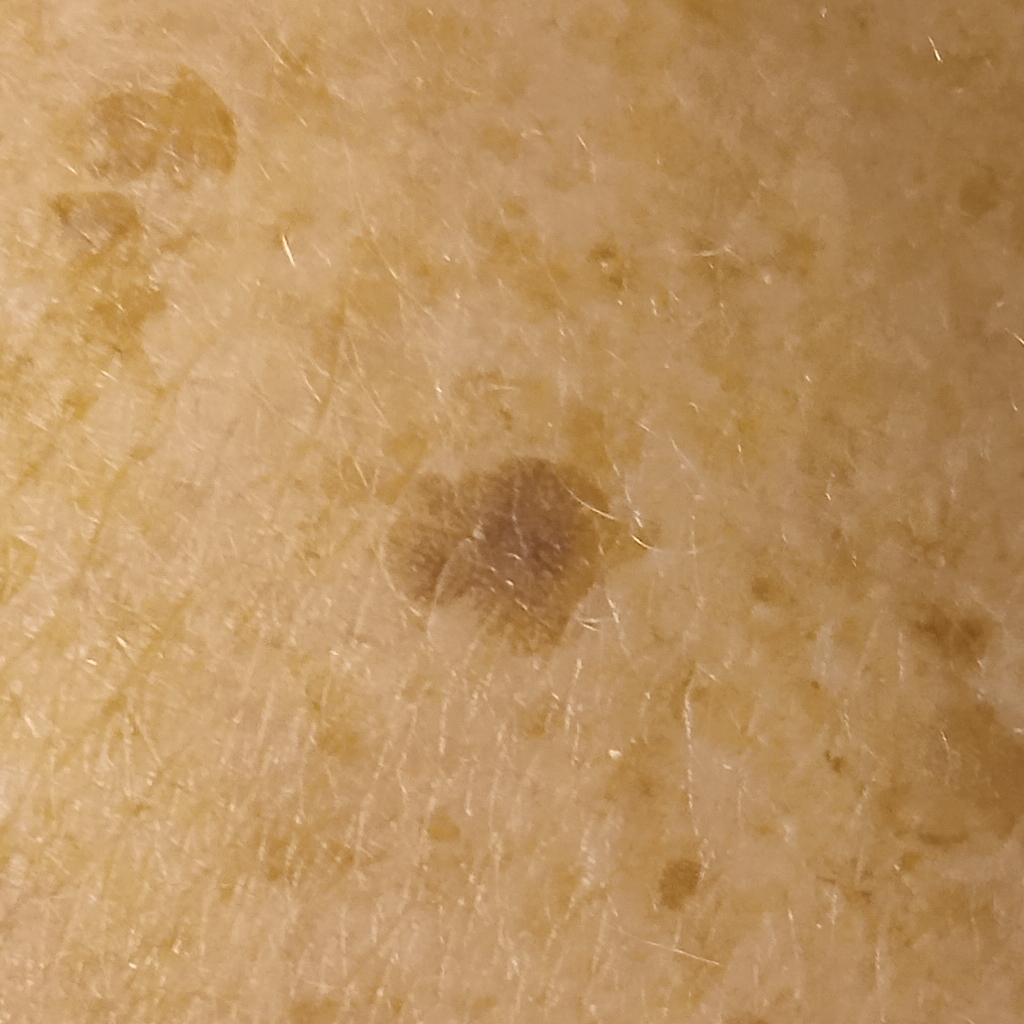Conclusion: The consensus diagnosis for this lesion was a seborrheic keratosis.